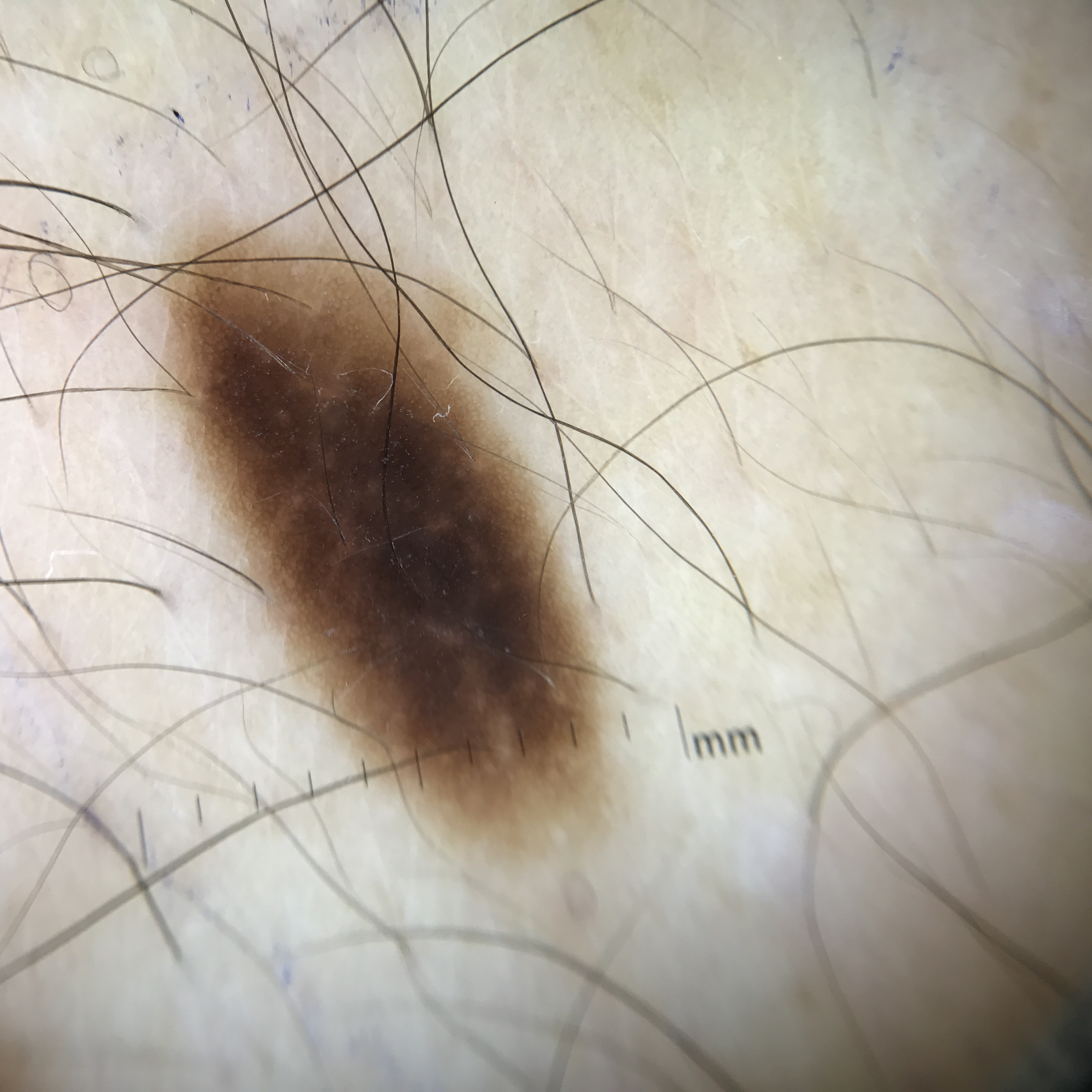Case:
• image type — dermatoscopy
• label — dysplastic junctional nevus (expert consensus)